The affected area is the head or neck · close-up view · the patient is 18–29, female — 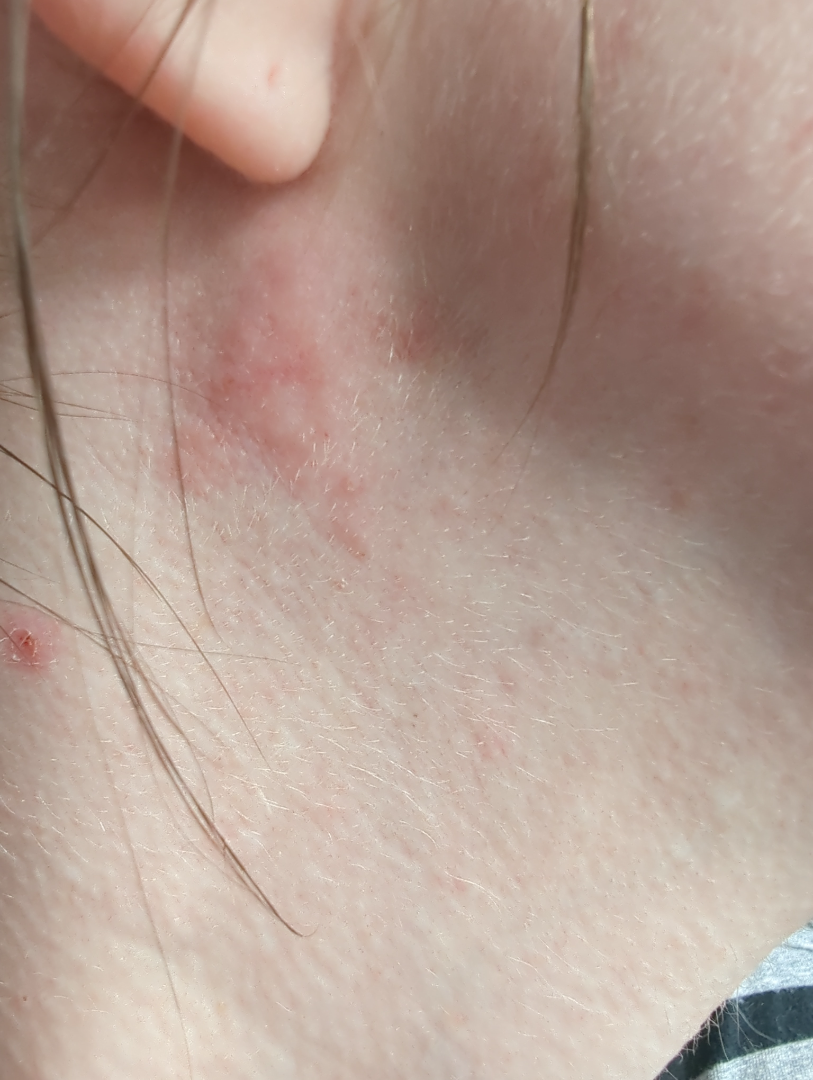Symptoms reported: bothersome appearance, enlargement, pain and itching.
Self-categorized by the patient as a rash.
The contributor reports the lesion is raised or bumpy.
Present for less than one week.
Three independent reviewers: favoring Acne; also consider Seborrheic Dermatitis; also raised was Allergic Contact Dermatitis.